A dermoscopic close-up of a skin lesion.
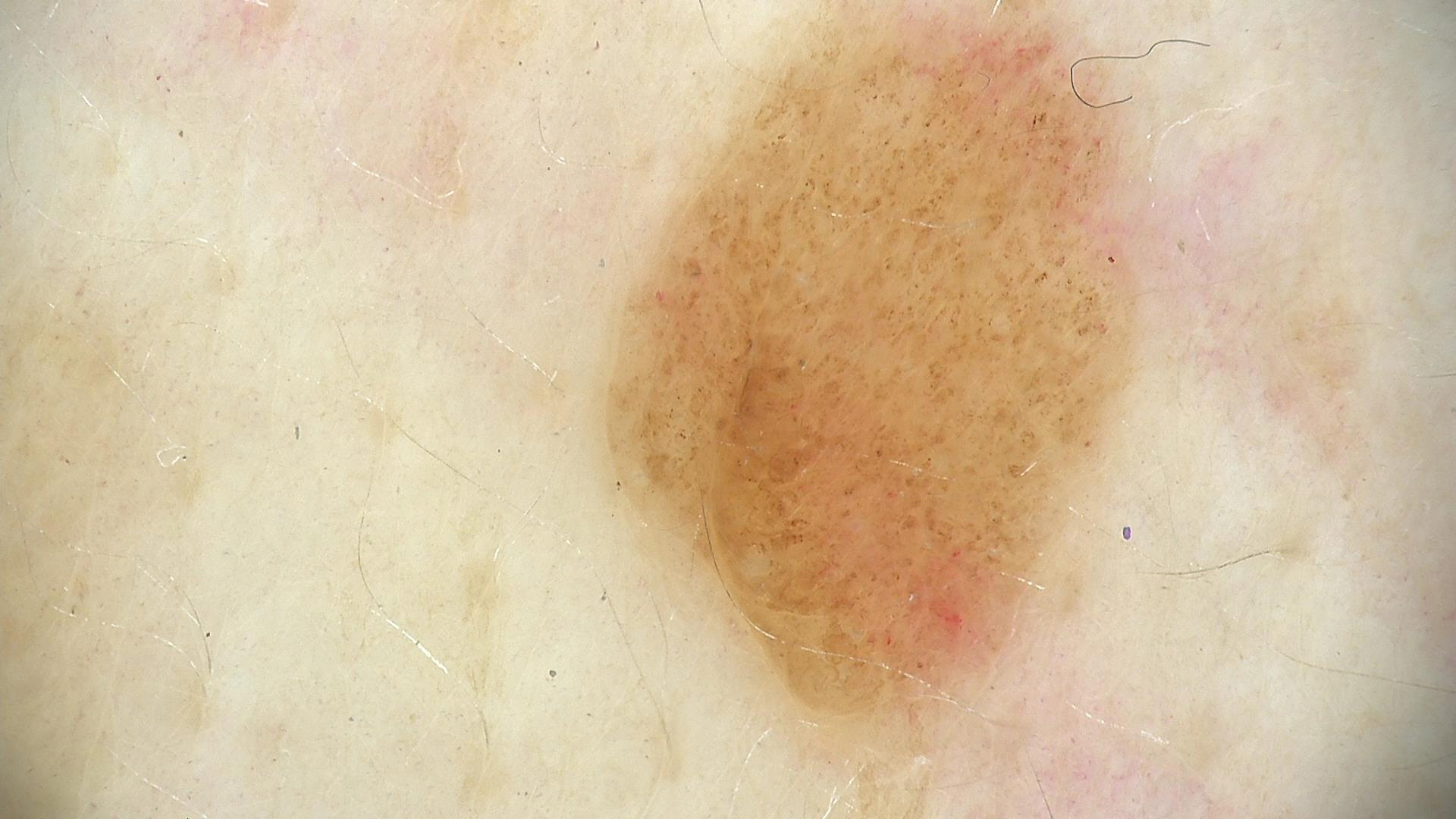This is a banal lesion. Diagnosed as a compound nevus.